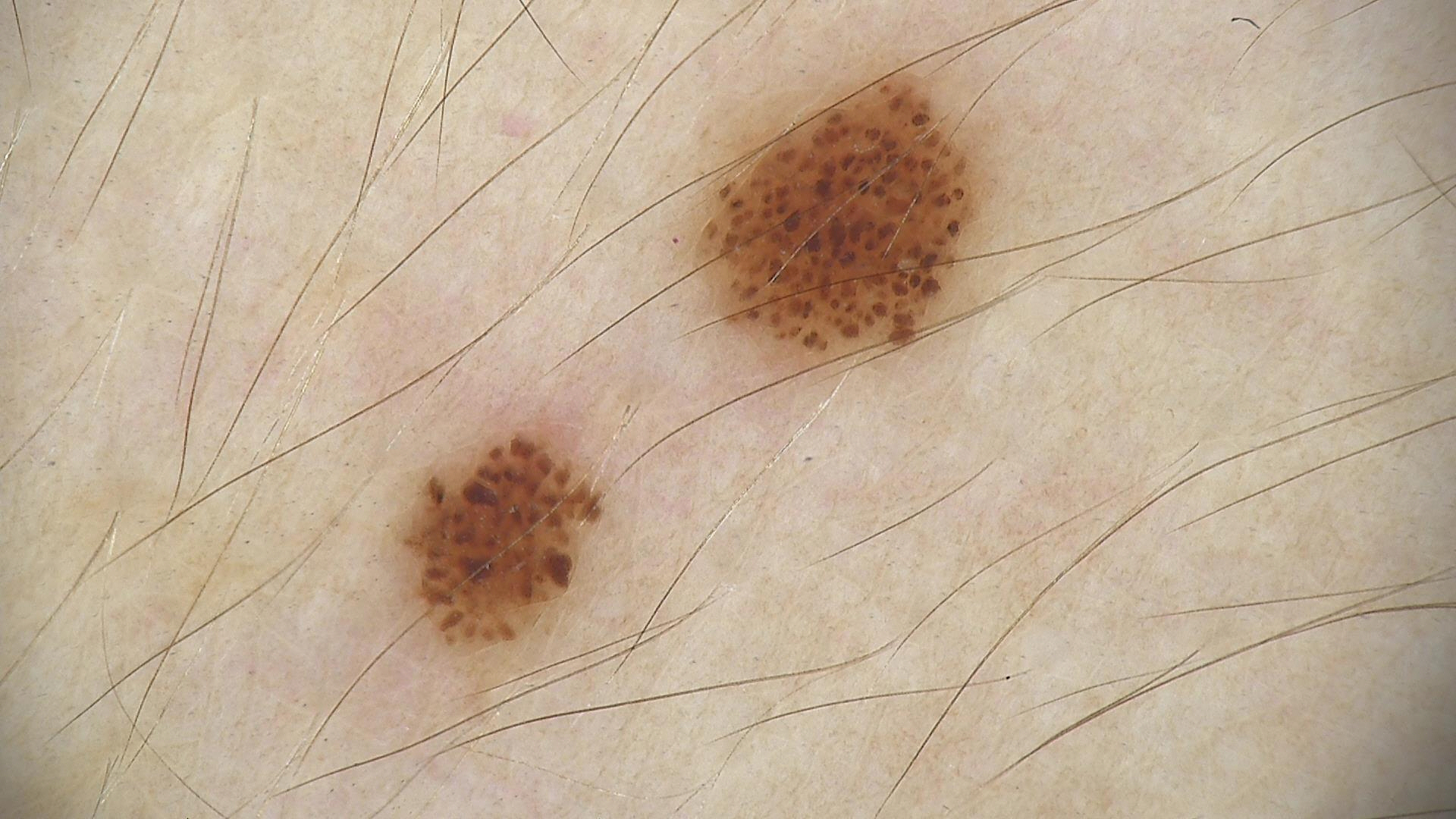Conclusion: Diagnosed as a benign lesion — a dysplastic junctional nevus.